A dermoscopic close-up of a skin lesion.
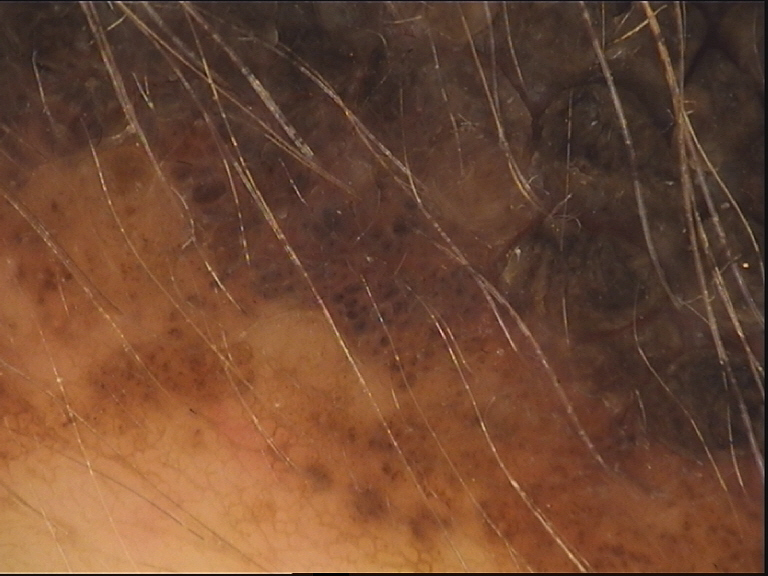subtype = banal, diagnostic label = congenital compound nevus (expert consensus).